The patient reports the lesion is fluid-filled, rough or flaky and raised or bumpy · reported lesion symptoms include enlargement, bothersome appearance and itching · skin tone: Fitzpatrick skin type V; non-clinician graders estimated Monk Skin Tone 6 or 8 (two reviewer pools disagreed) · no constitutional symptoms were reported · located on the arm · the photo was captured at a distance — 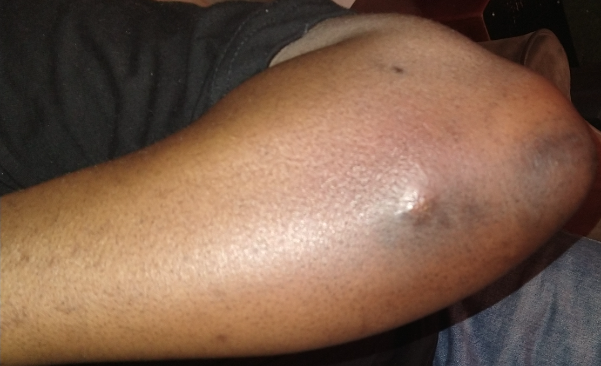The case was difficult to assess from the available photograph.